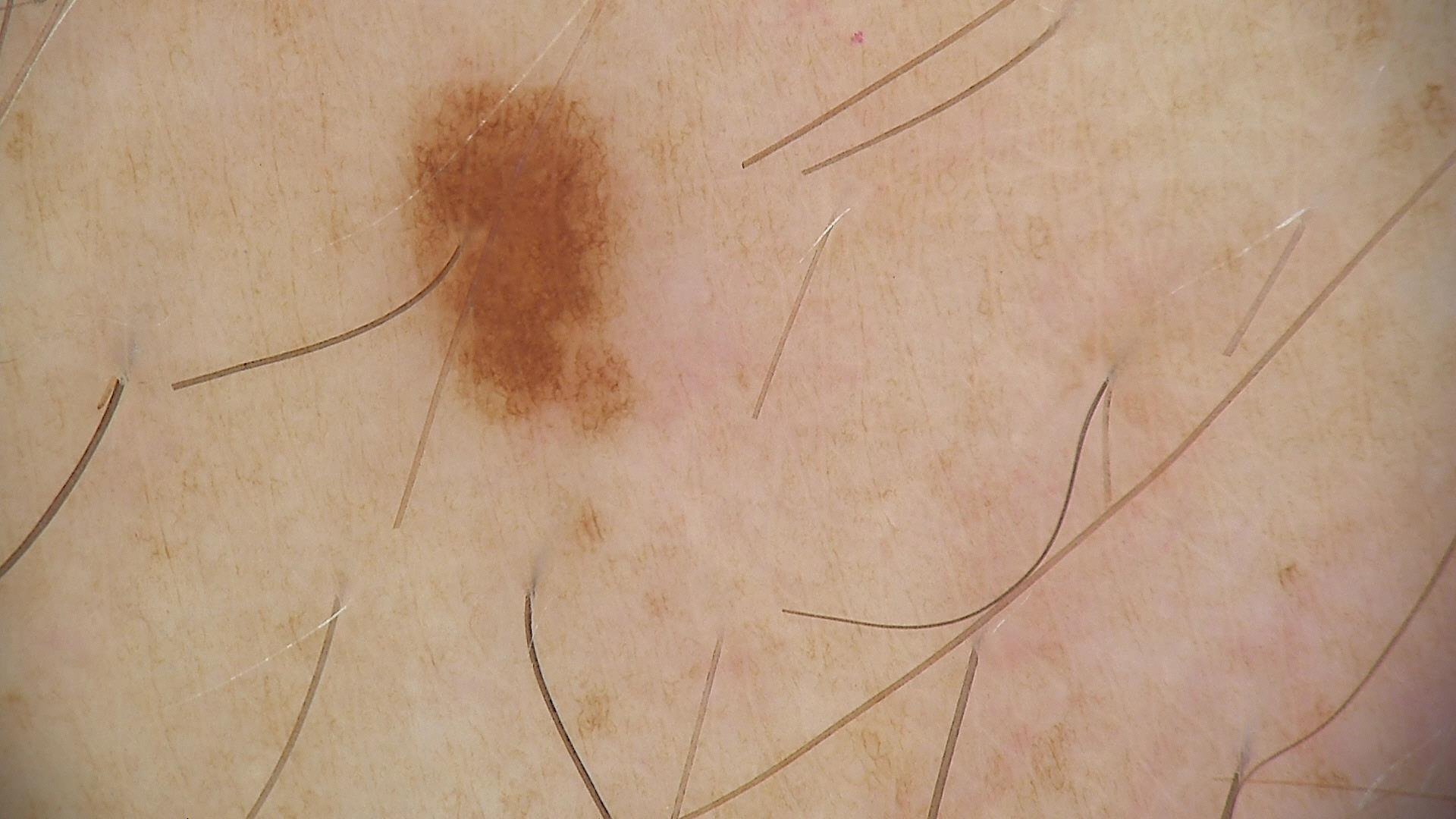Q: What is the imaging modality?
A: dermatoscopy
Q: What is this lesion?
A: dysplastic junctional nevus (expert consensus)